Dermoscopy of a skin lesion.
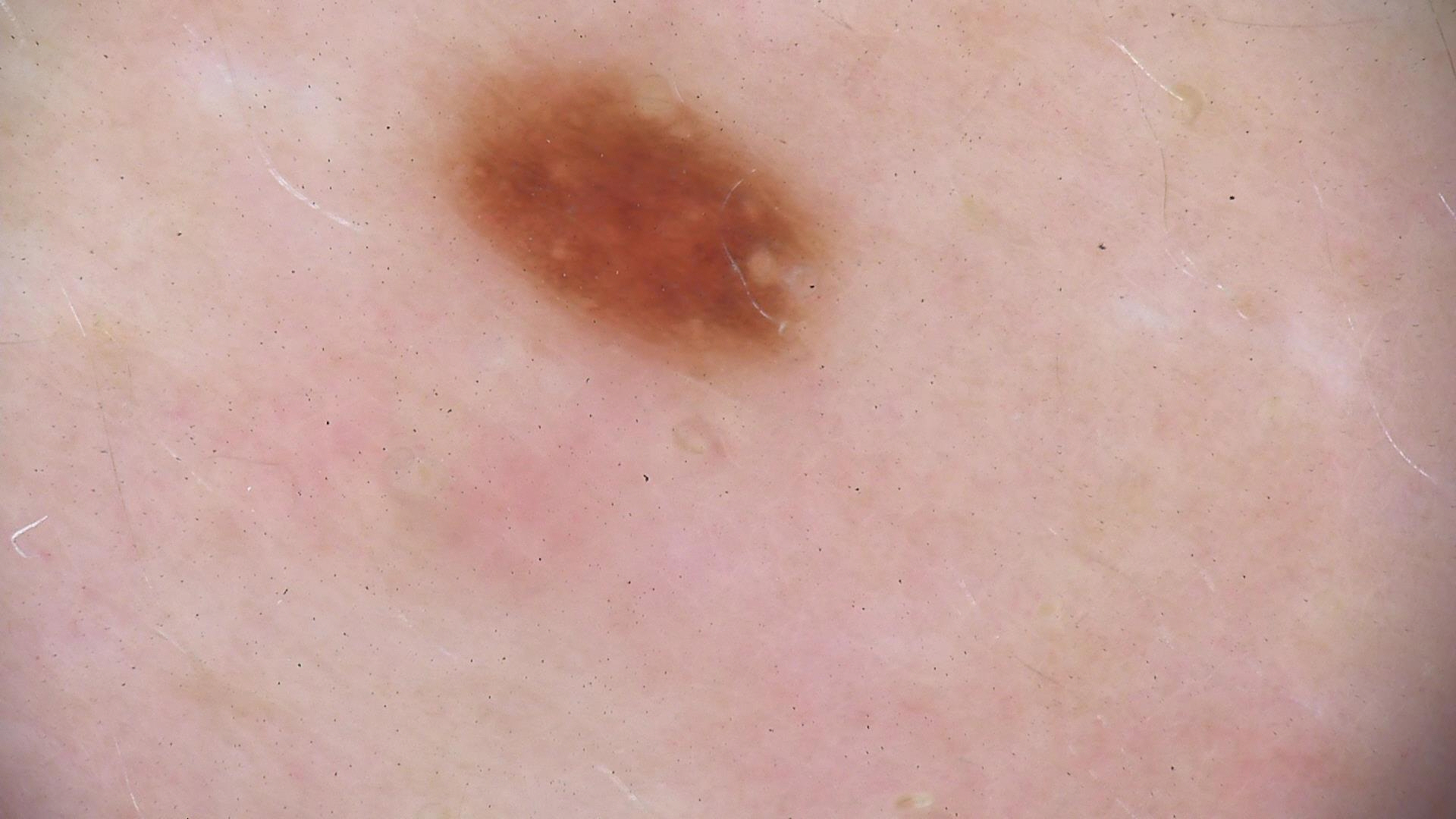Consistent with a dysplastic junctional nevus.